The photograph is a close-up of the affected area: 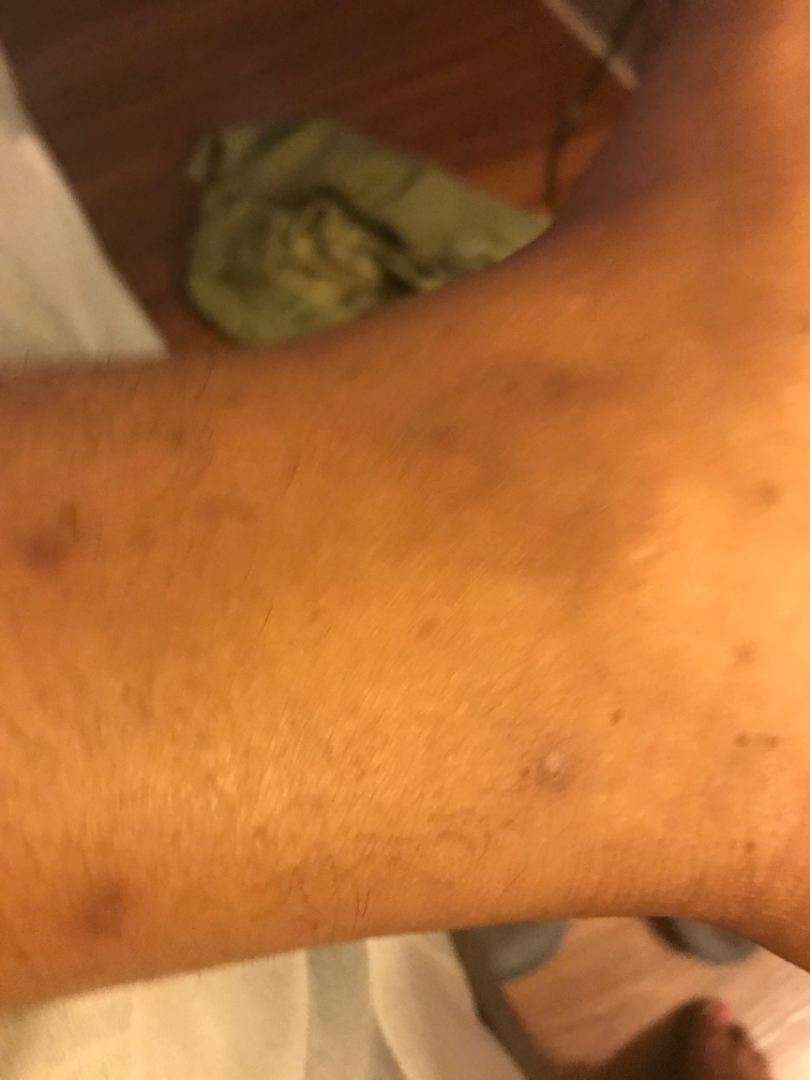<summary>
  <assessment>not assessable</assessment>
</summary>